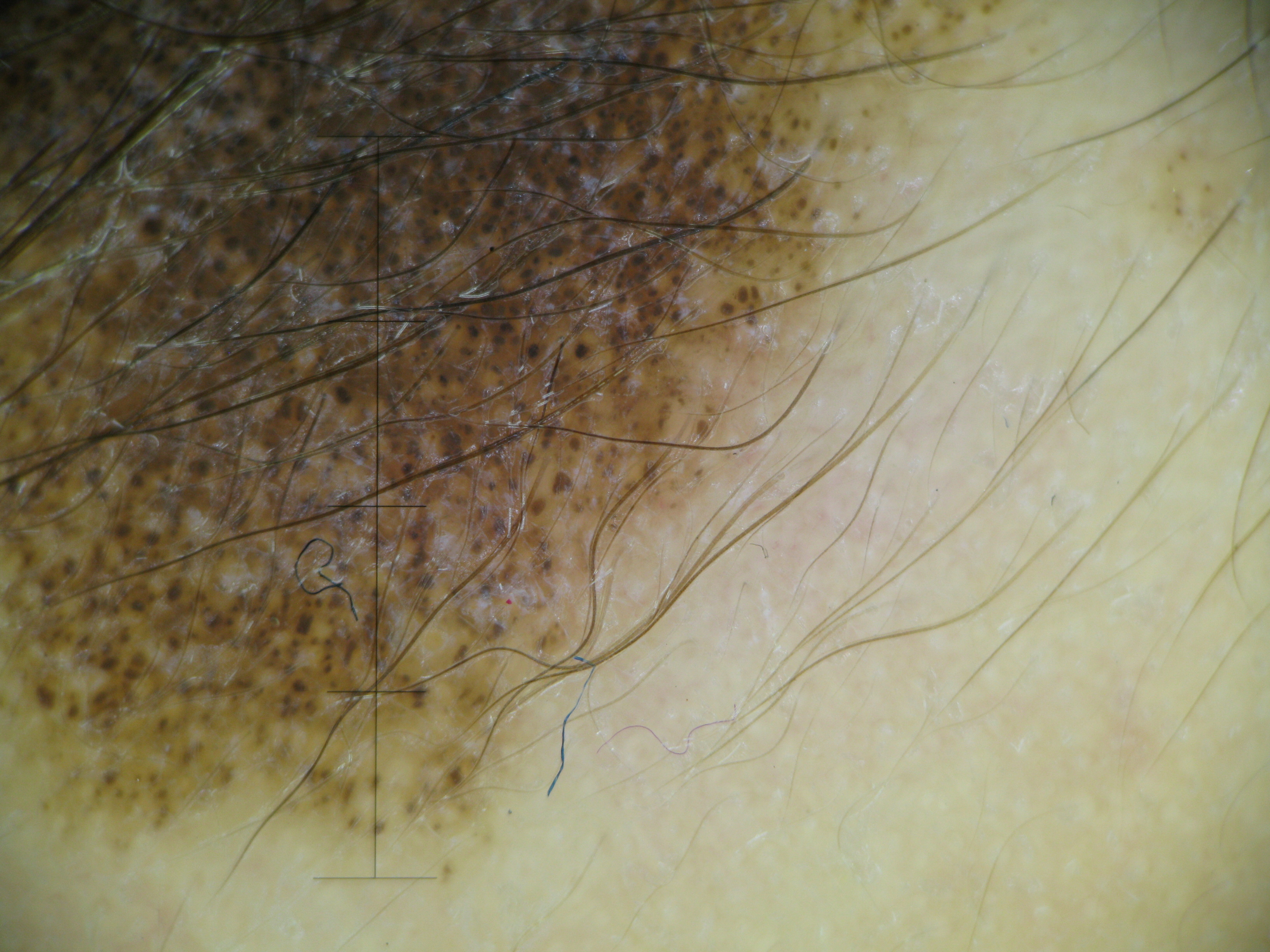A dermoscopic close-up of a skin lesion.
The architecture is that of a banal lesion.
Consistent with a congenital compound nevus.